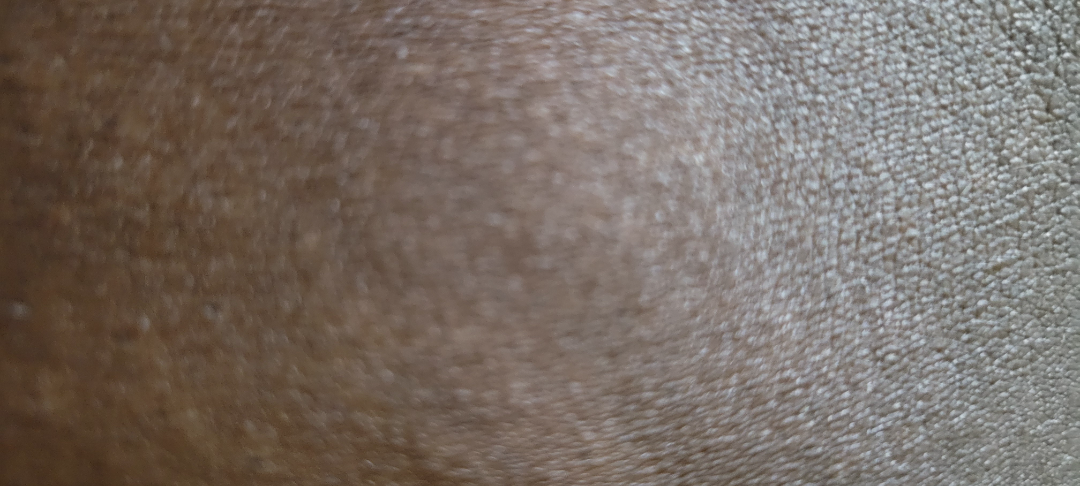<case>
  <assessment>could not be assessed</assessment>
  <systemic_symptoms>none reported</systemic_symptoms>
  <texture>raised or bumpy</texture>
  <duration>less than one week</duration>
  <symptoms>bothersome appearance, pain</symptoms>
  <patient_category>a rash</patient_category>
  <shot_type>at a distance</shot_type>
</case>